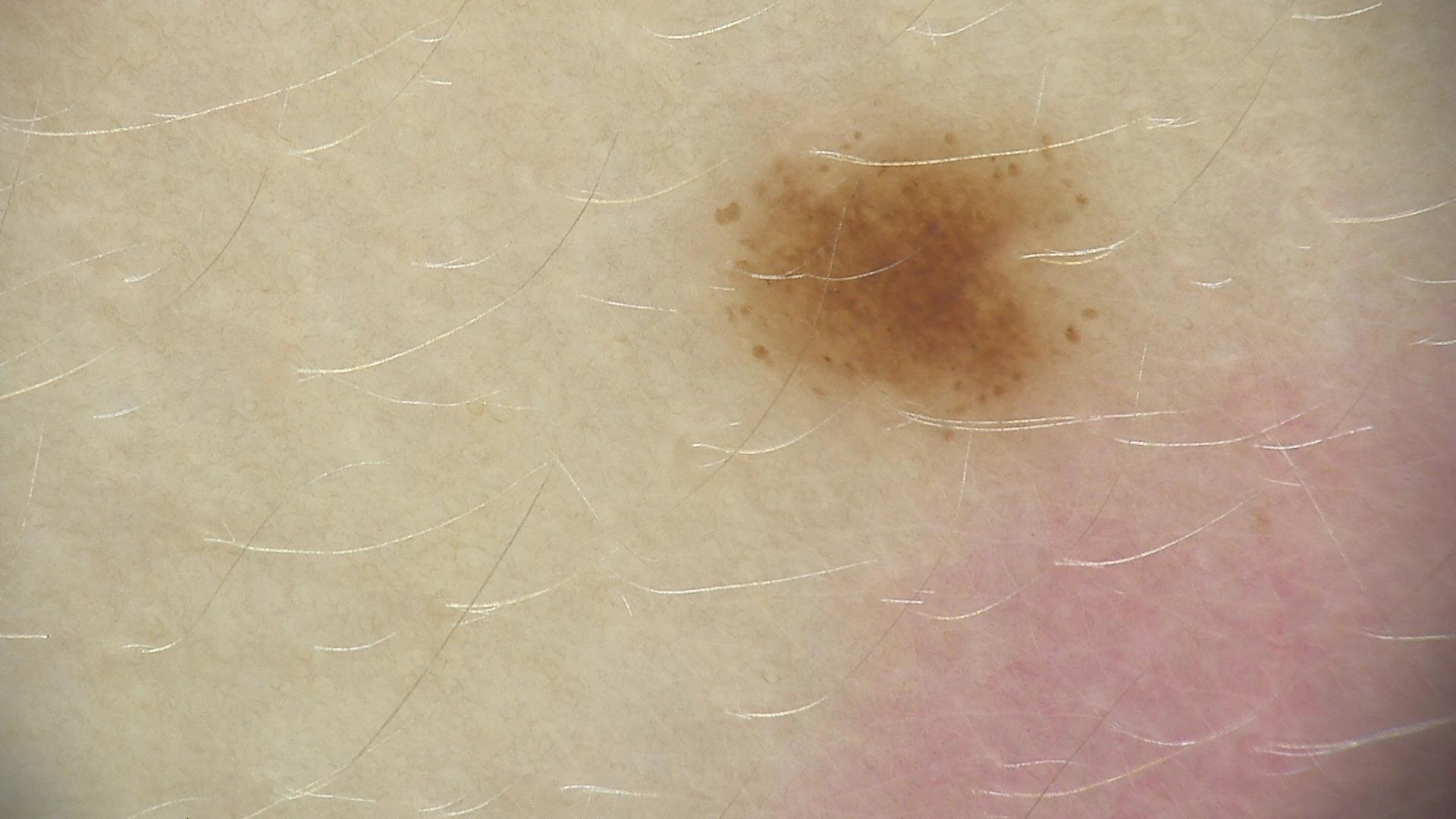A dermoscopic photograph of a skin lesion.
Classified as a dysplastic junctional nevus.